The photo was captured at an angle:
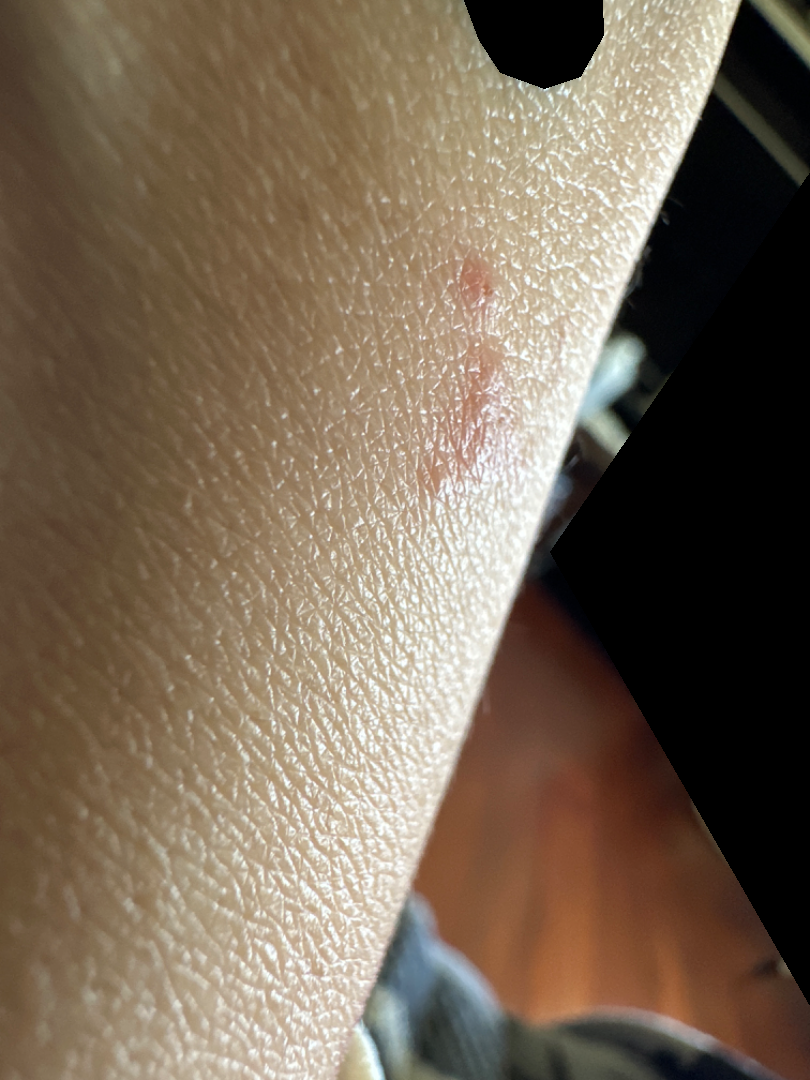• impression · one reviewing dermatologist: the leading consideration is Allergic Contact Dermatitis; an alternative is Eczema